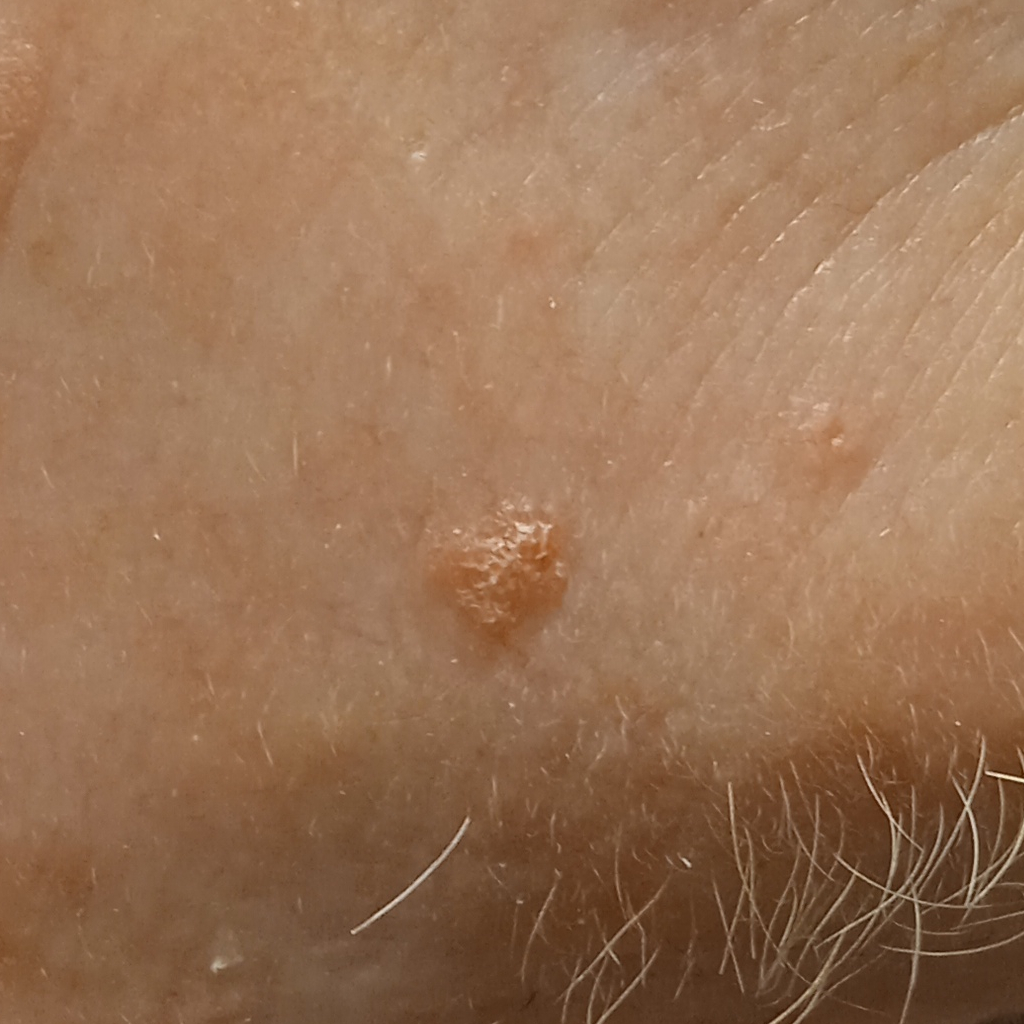referral: research study (no referral diagnosis)
mole_burden: a moderate number of melanocytic nevi
sun_reaction: skin reddens with sun exposure
patient:
  age: 77
  sex: male
lesion_location: the face
lesion_size:
  diameter_mm: 4.3
diagnosis:
  name: actinic keratosis
  malignancy: benign